The photograph was taken at an angle; the affected area is the leg; the patient is 30–39, male: 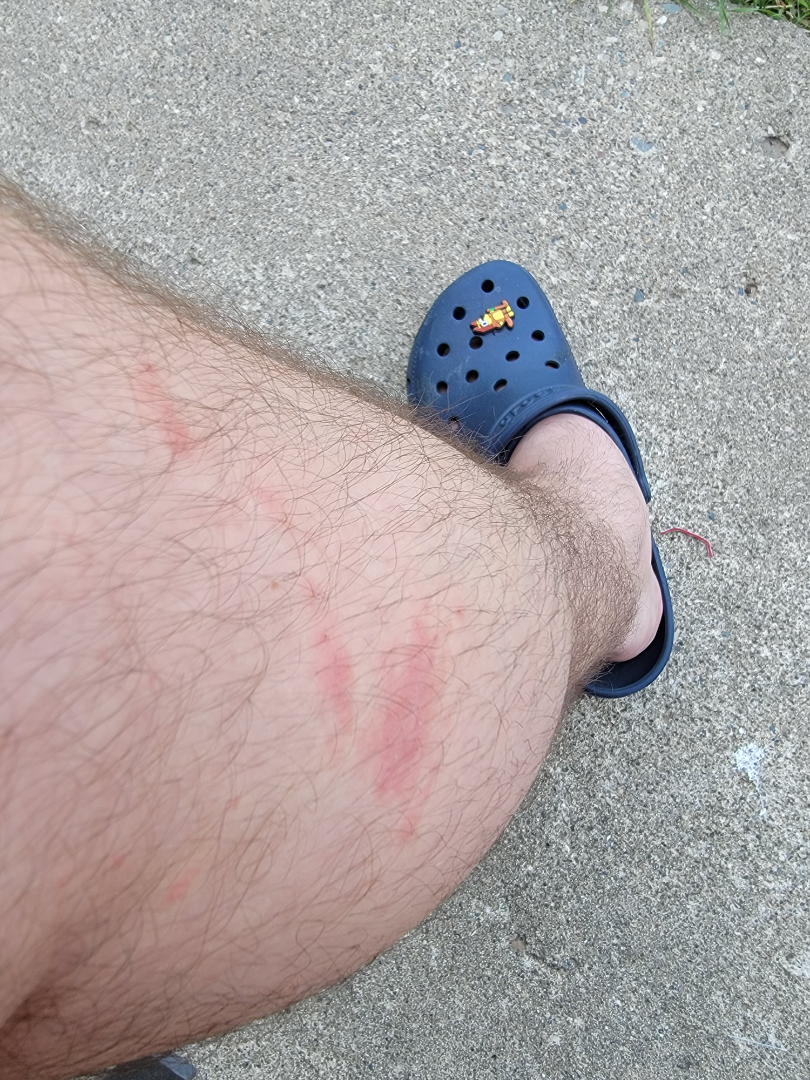<dermatology_case>
<assessment>indeterminate</assessment>
</dermatology_case>